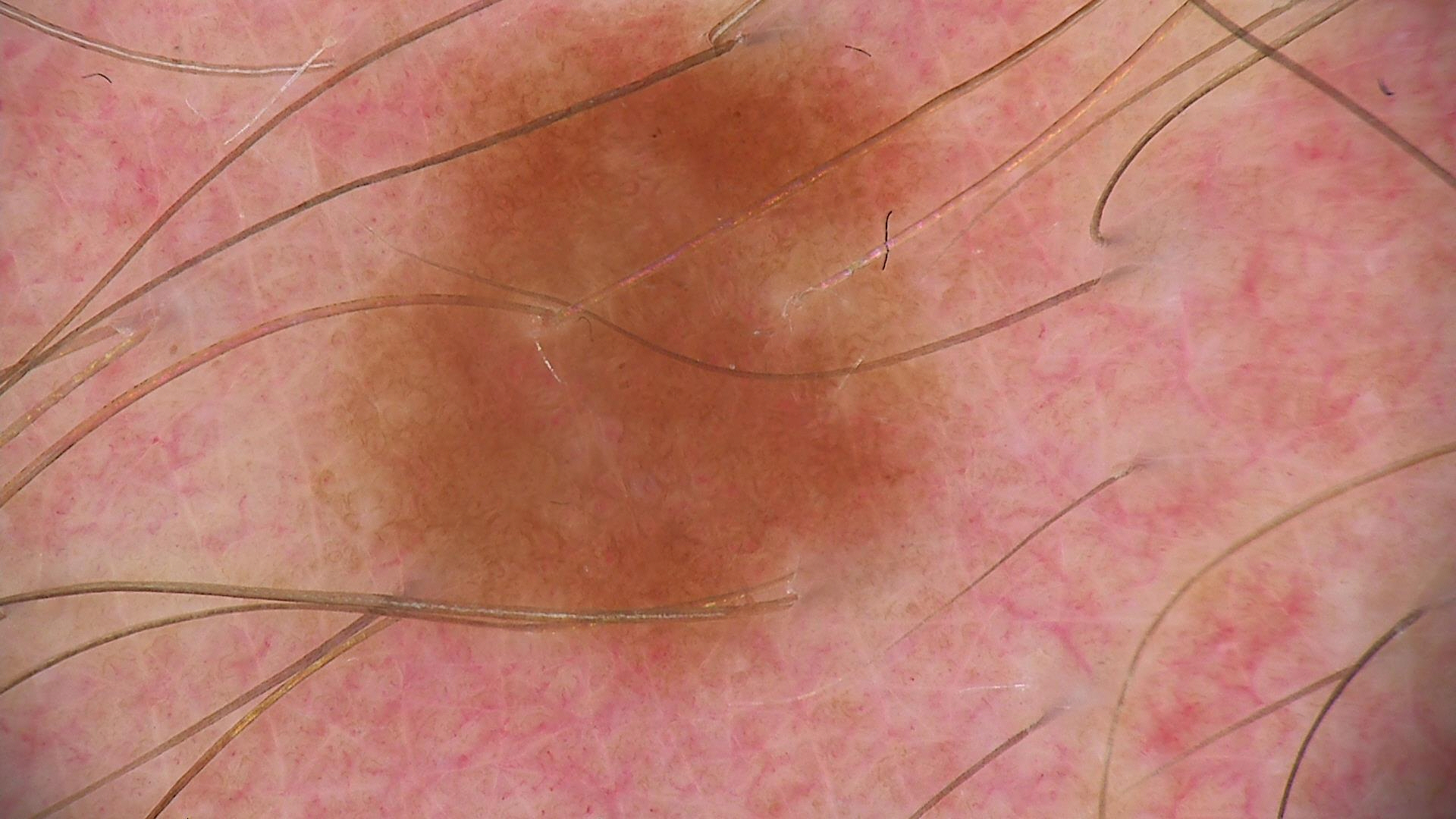Dermoscopy of a skin lesion. Diagnosed as a benign lesion — a dysplastic junctional nevus.